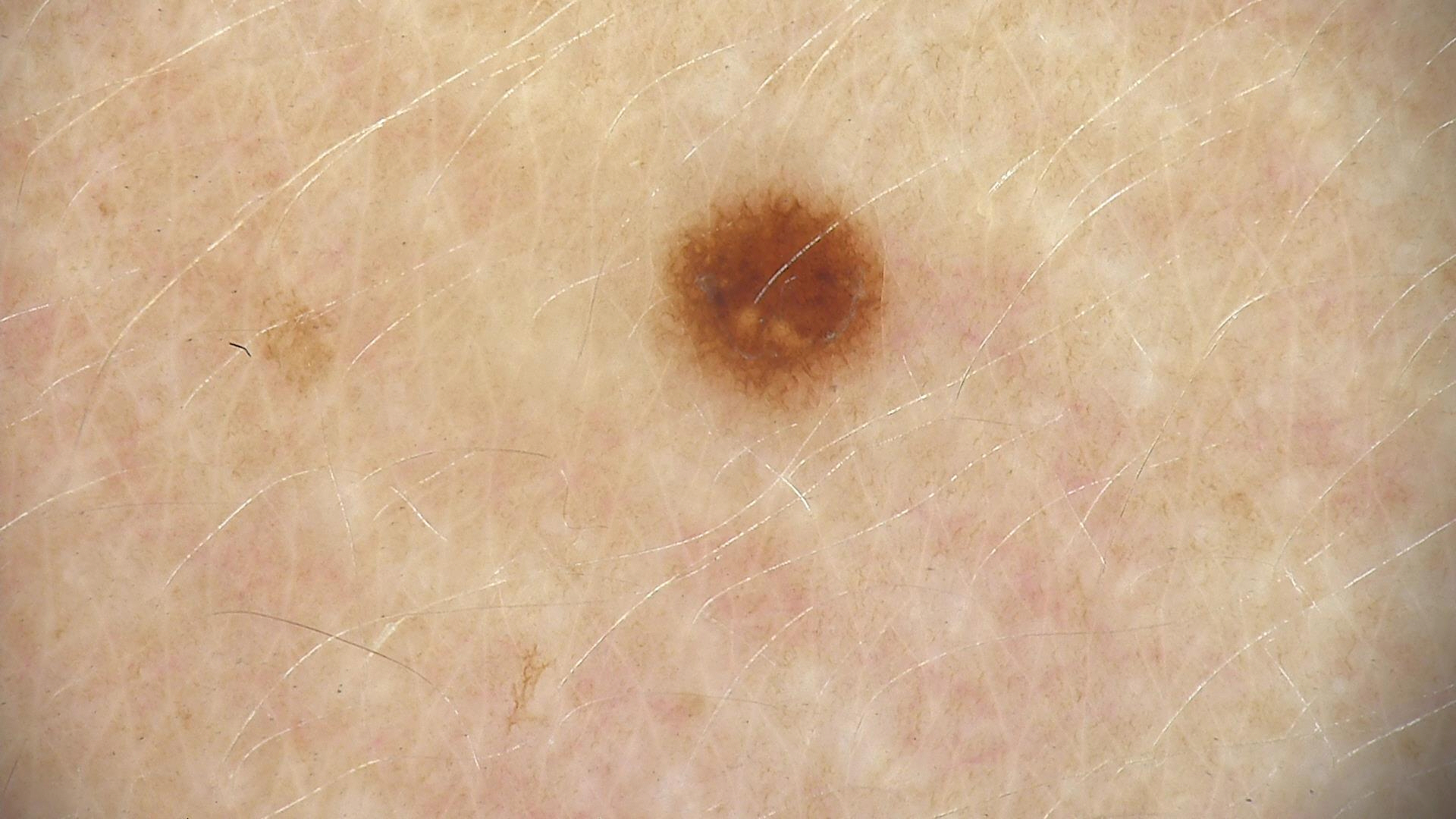imaging = dermoscopy | diagnosis = dysplastic junctional nevus (expert consensus).